Reported lesion symptoms include bothersome appearance, this is a close-up image, the subject is a female aged 60–69, the patient reports the lesion is raised or bumpy.
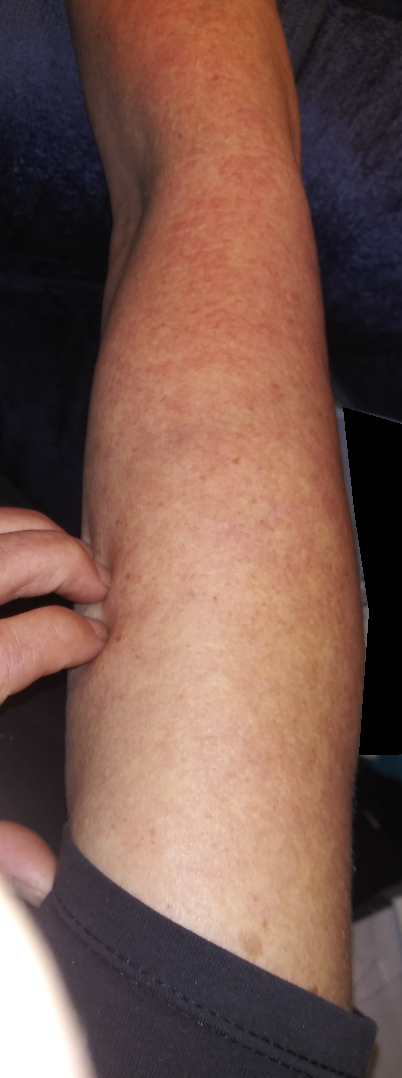The reviewing dermatologist was unable to assign a differential diagnosis from the image.